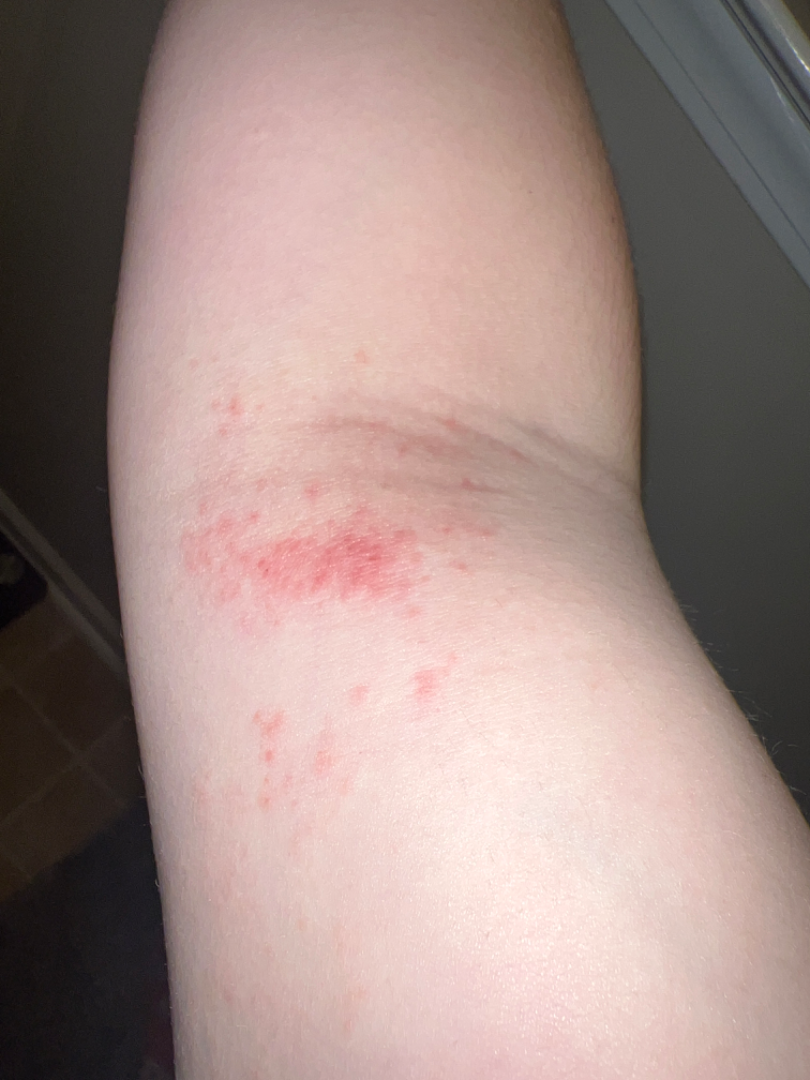Q: Patient demographics?
A: female, age 18–29
Q: Image view?
A: close-up
Q: What is the affected area?
A: arm
Q: Texture?
A: raised or bumpy
Q: What is the patient's skin tone?
A: Fitzpatrick II
Q: What is the differential diagnosis?
A: consistent with Eczema